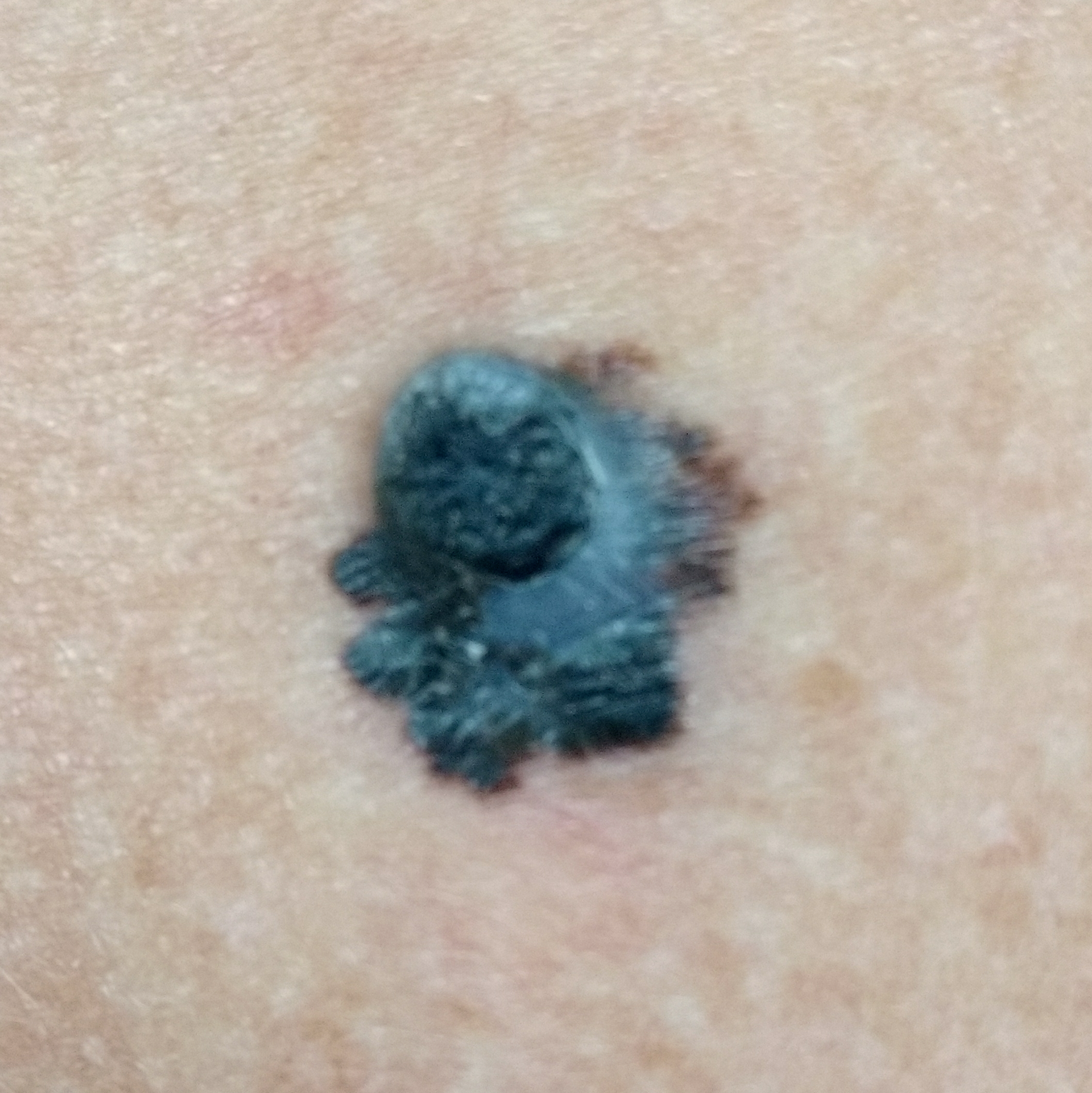risk factors = prior malignancy (patient or family), alcohol use; diagnosis = melanoma (biopsy-proven).